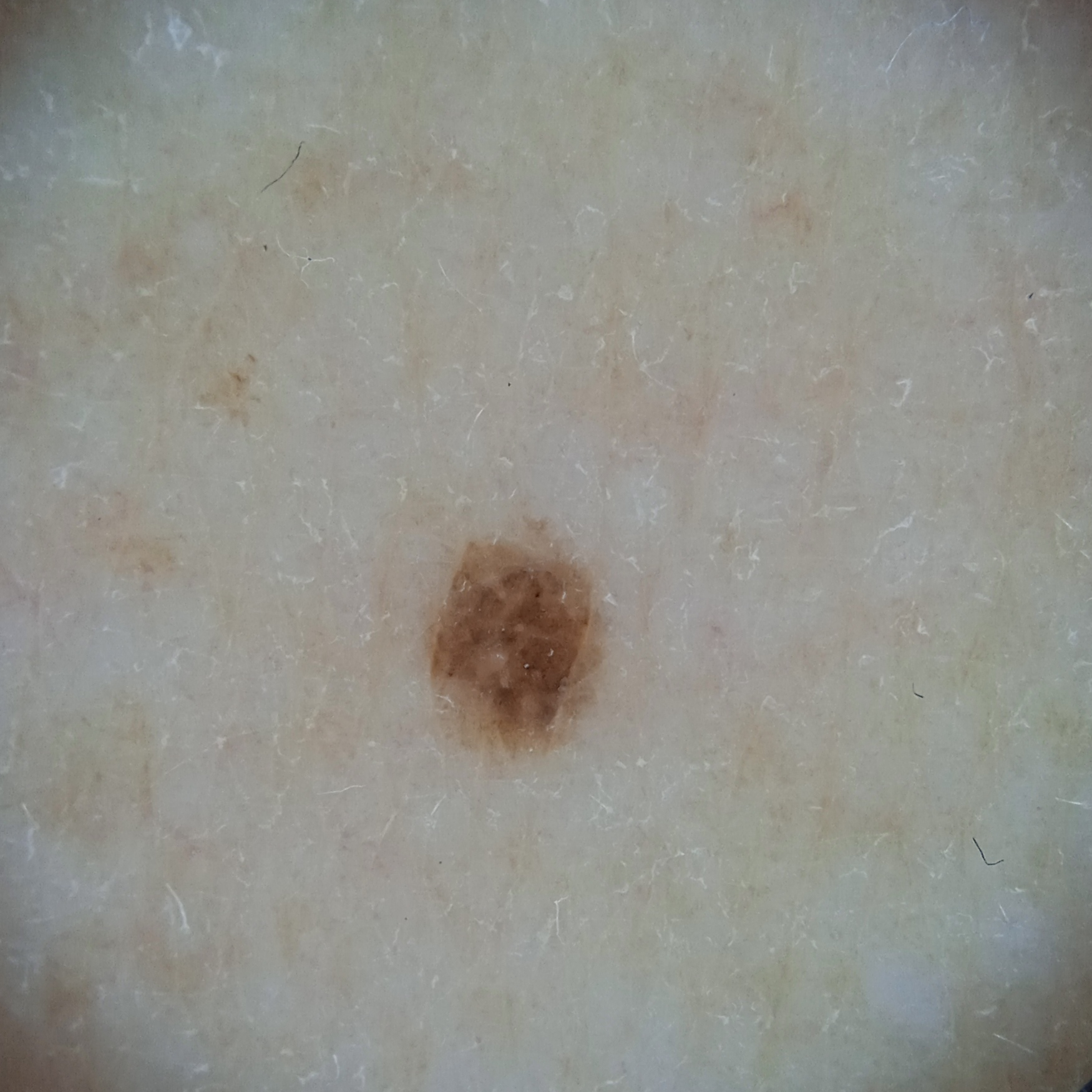  mole_burden: a moderate number of melanocytic nevi
  sun_reaction: skin reddens with sun exposure
  referral: research study (no referral diagnosis)
  lesion_location: an arm
  lesion_size:
    diameter_mm: 2.5
  diagnosis:
    name: melanocytic nevus
    malignancy: benign